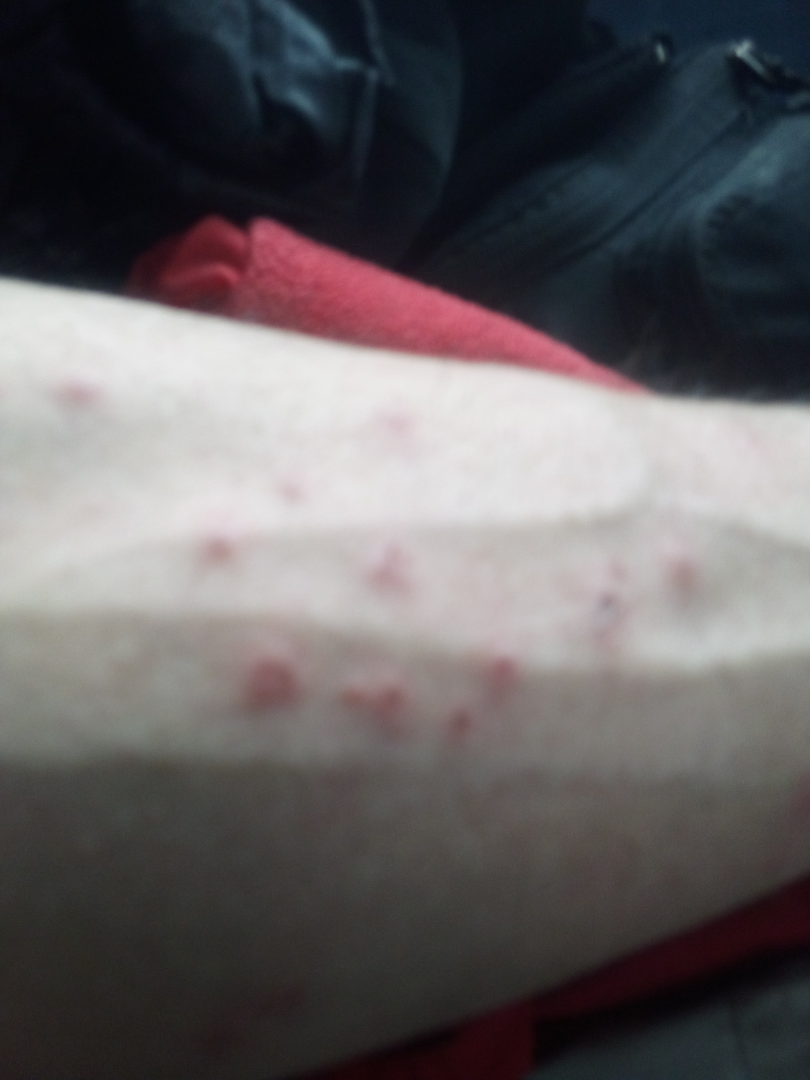The reviewing dermatologist was unable to assign a differential diagnosis from the image. The contributor reports the lesion is raised or bumpy. The subject is male. Associated systemic symptoms include fatigue. The condition has been present for less than one week. The patient described the issue as a rash. Reported lesion symptoms include enlargement, bothersome appearance and itching. Located on the leg and arm. The photo was captured at an angle.